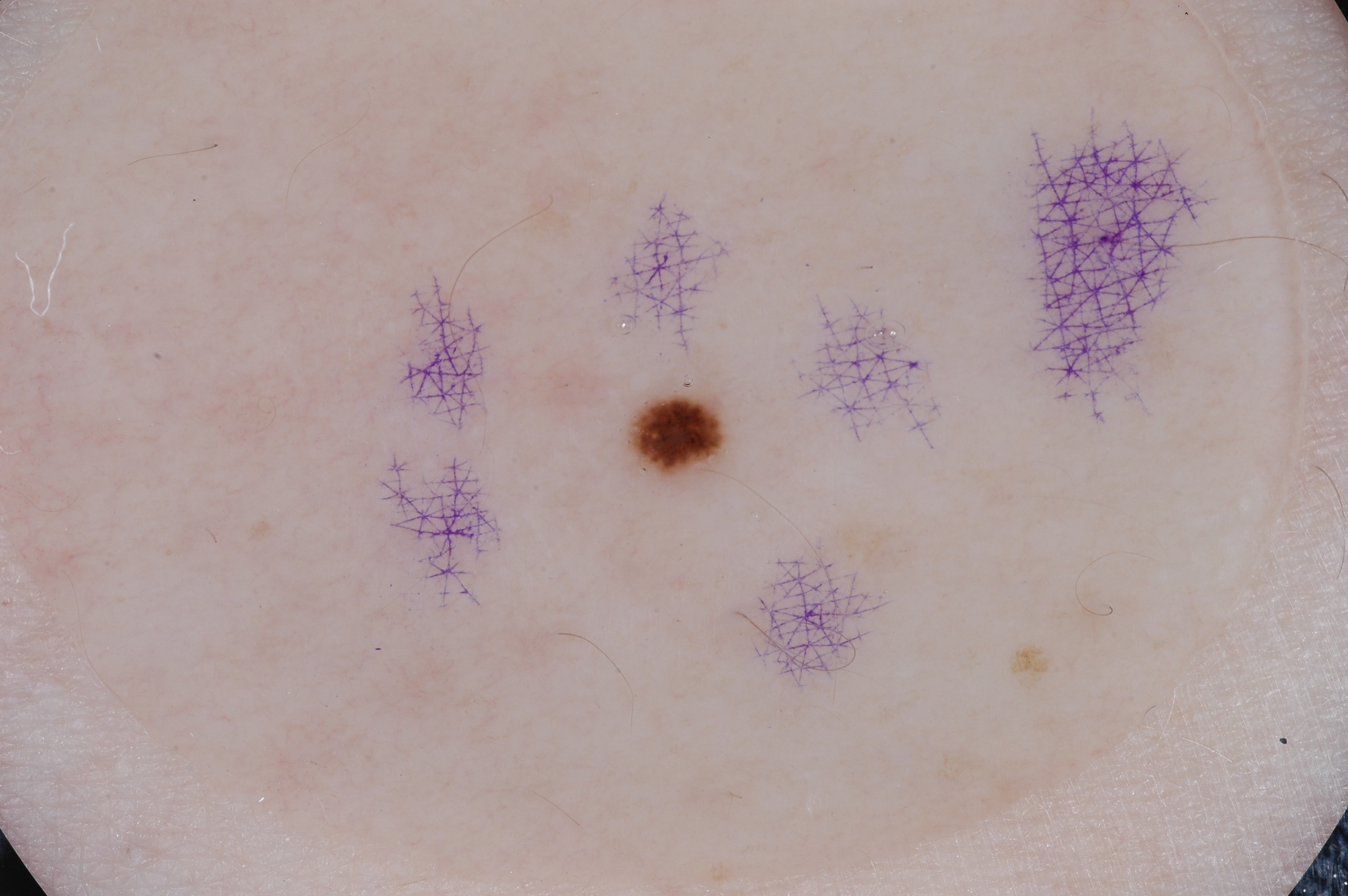A skin lesion imaged with a dermatoscope.
The dermoscopic pattern shows milia-like cysts, with no streaks, pigment network, or negative network.
The lesion takes up about 1% of the image.
The lesion spans x1=643 y1=392 x2=726 y2=468.
Clinically diagnosed as a melanocytic nevus.